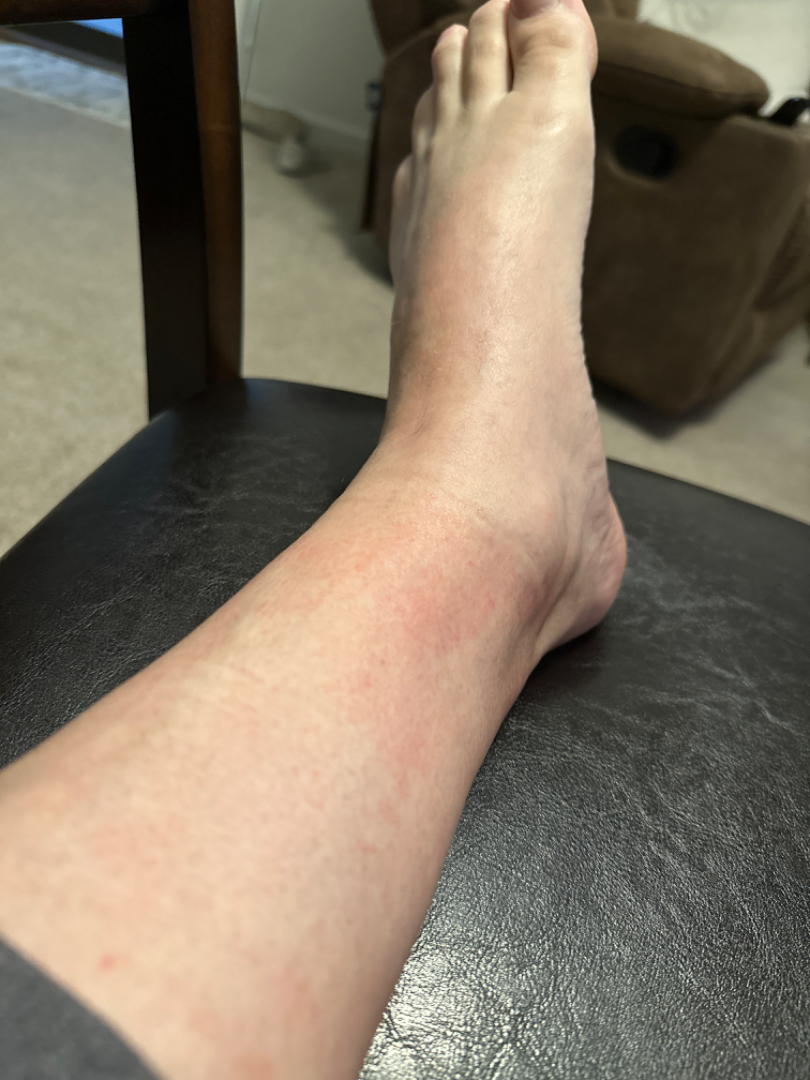The case was difficult to assess from the available photograph. The patient described the issue as skin that appeared healthy to them. The condition has been present for one to four weeks. Reported lesion symptoms include itching, burning and bothersome appearance. The photograph was taken at an angle. Located on the leg and top or side of the foot. The lesion is described as rough or flaky and flat.